A female patient aged 28 to 32. This is a dermoscopic photograph of a skin lesion:
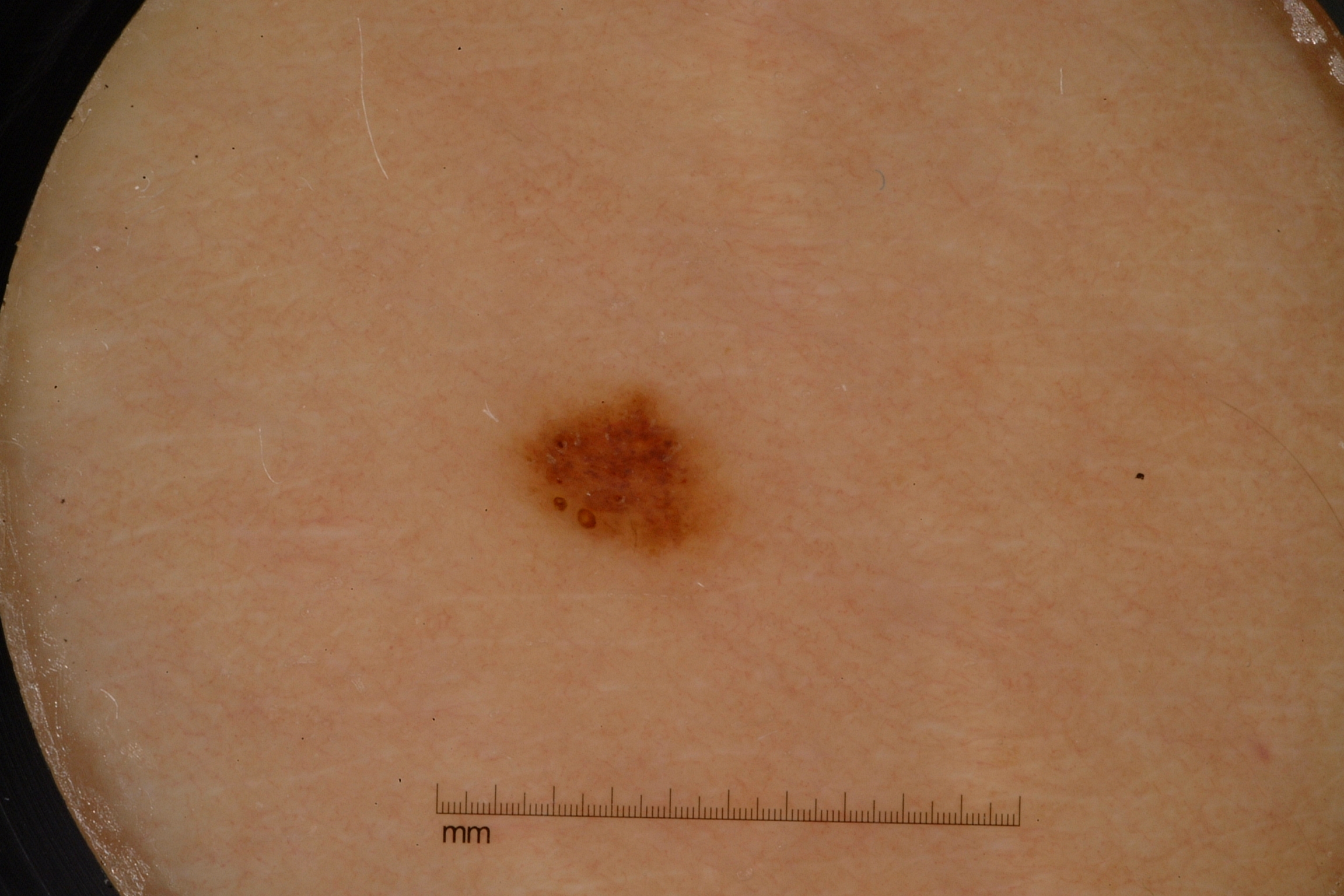Dermoscopic assessment notes no streaks, pigment network, negative network, or milia-like cysts.
In (x1, y1, x2, y2) order, the lesion's extent is bbox(507, 386, 733, 565).
Expert review diagnosed this as a melanocytic nevus.